An image taken at an angle, the patient described the issue as a rash, the affected area is the front of the torso and arm, the subject is a female aged 30–39, texture is reported as rough or flaky and raised or bumpy, the condition has been present for one to four weeks — 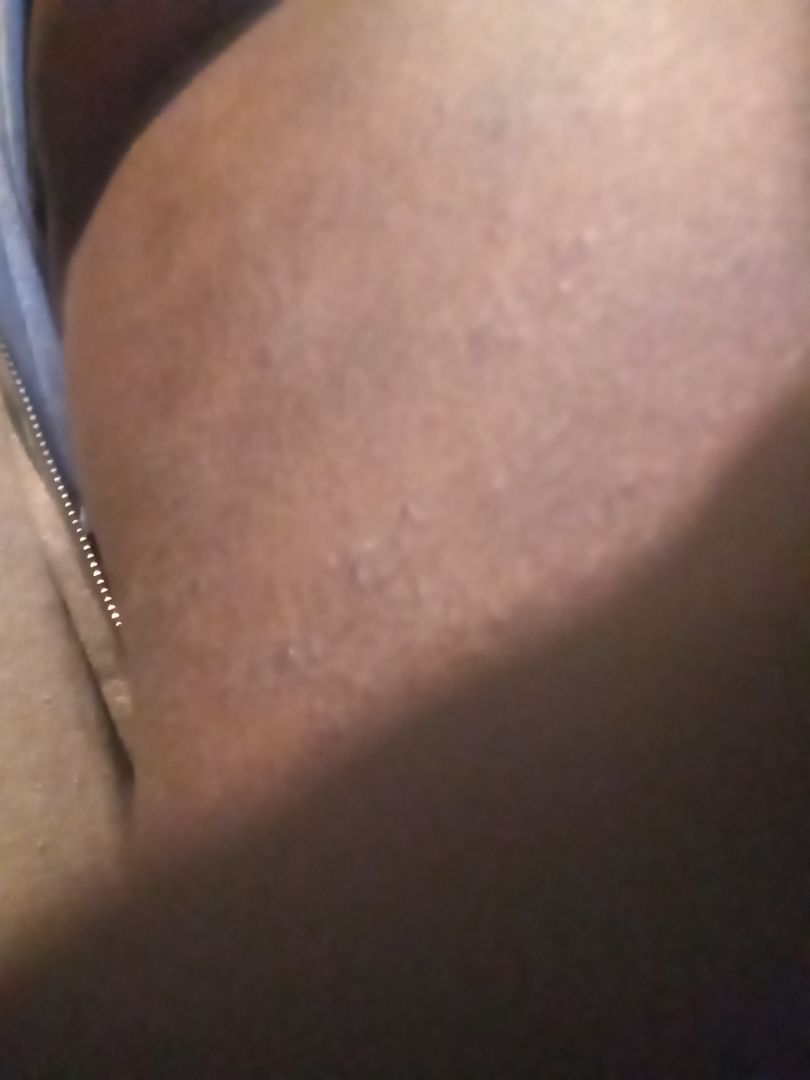The image was not sufficient for the reviewer to characterize the skin condition.